On a questionnaire the patient reported a family history of skin cancer, immunosuppression, and a personal history of skin cancer · dermoscopy of a skin lesion · the patient describes having numerous moles · a male subject age 65 · collected as part of a research study, without a referral diagnosis — 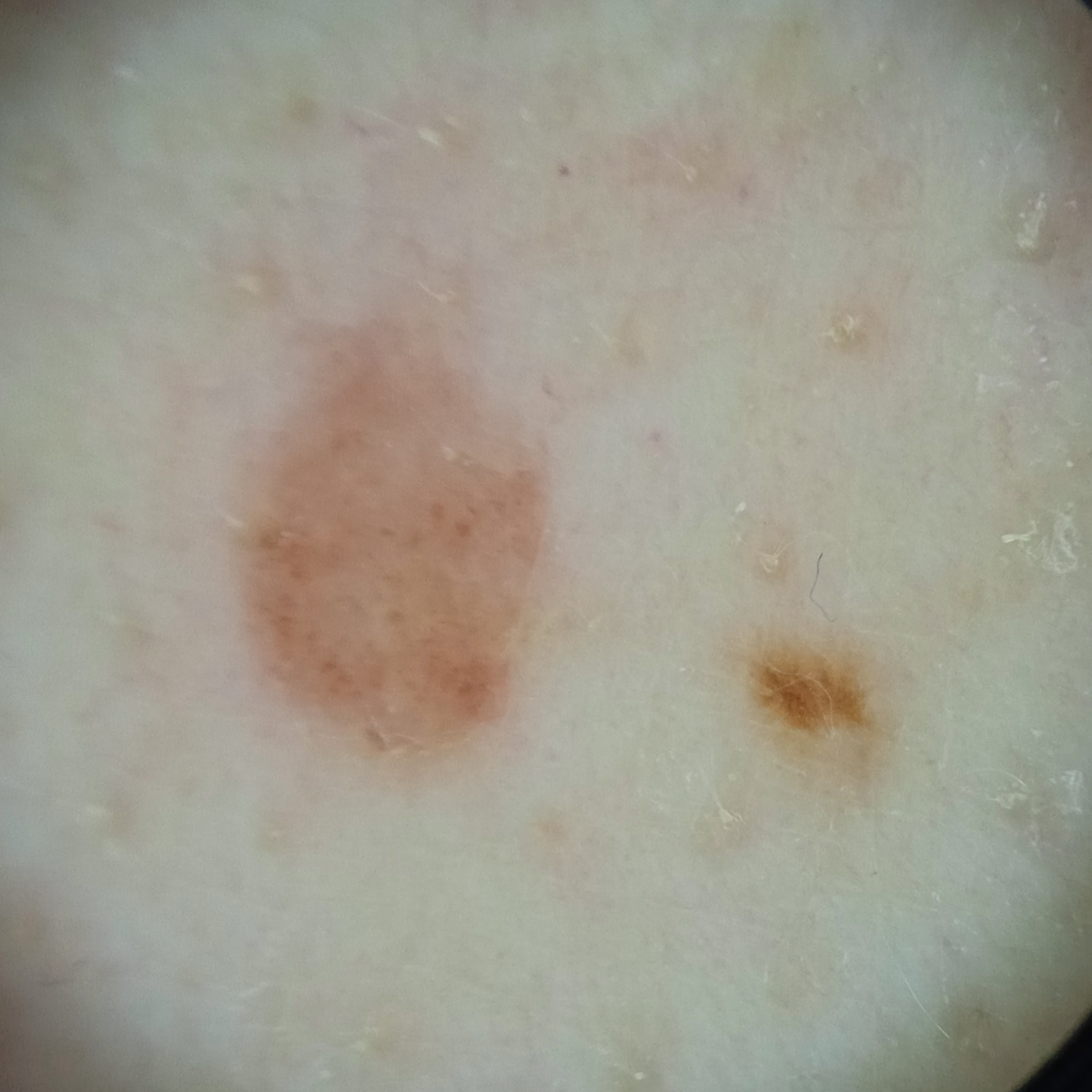Case summary:
The lesion is located on the back. Measuring roughly 4.4 mm.
Conclusion:
The consensus diagnosis for this lesion was a melanocytic nevus.